The arm is involved, the subject is a male aged 30–39, this image was taken at a distance.
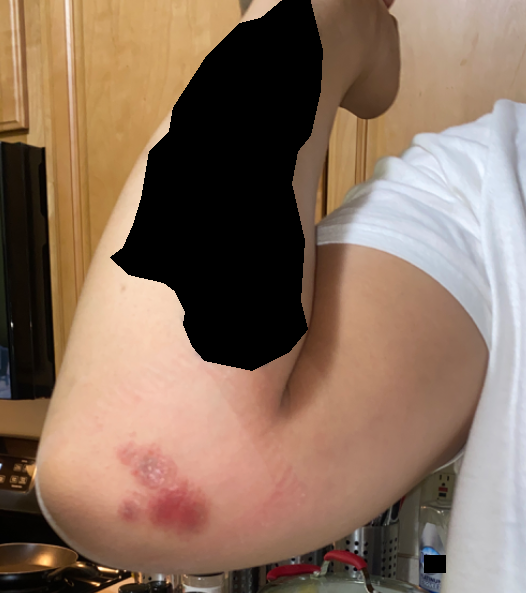Review: On dermatologist assessment of the image, most likely Herpes Zoster; also raised was Allergic Contact Dermatitis; less probable is Herpes Simplex.